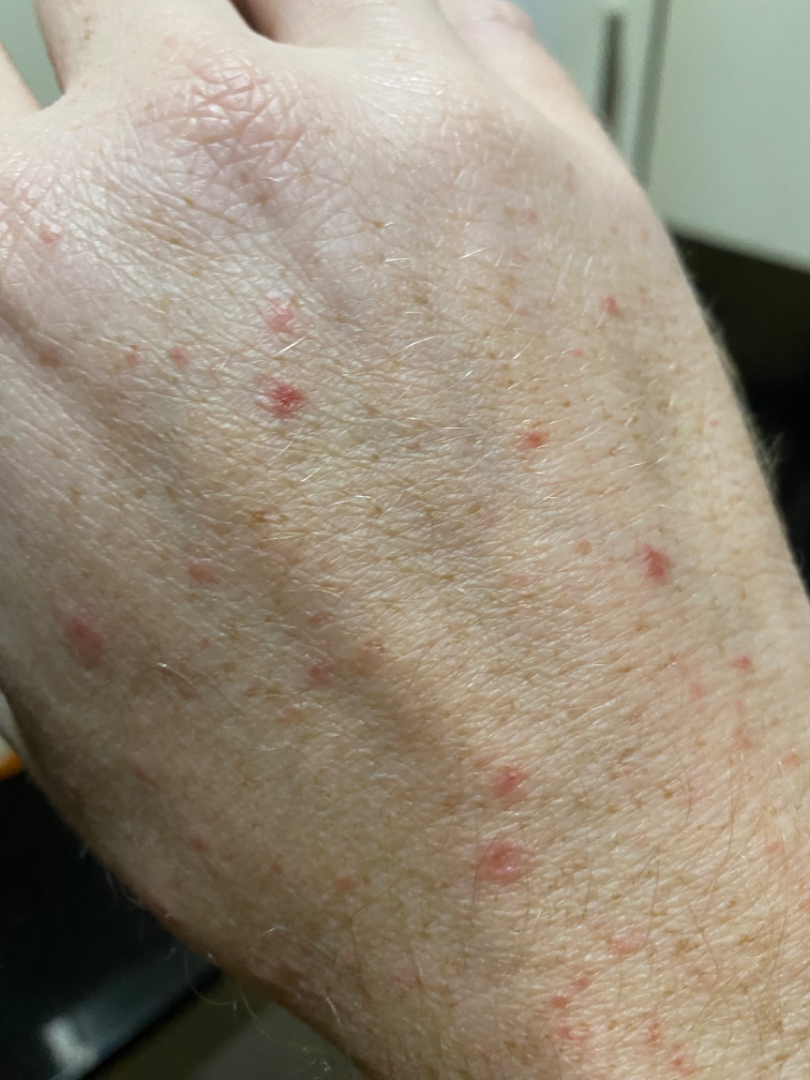contributor: male, age 40–49 | affected area: arm, palm and back of the hand | view: close-up | diagnostic considerations: Actinic Keratosis (weight 0.67); Psoriasis (weight 0.33).